The photograph was taken at an angle · symptoms reported: itching and burning · the affected area is the sole of the foot.
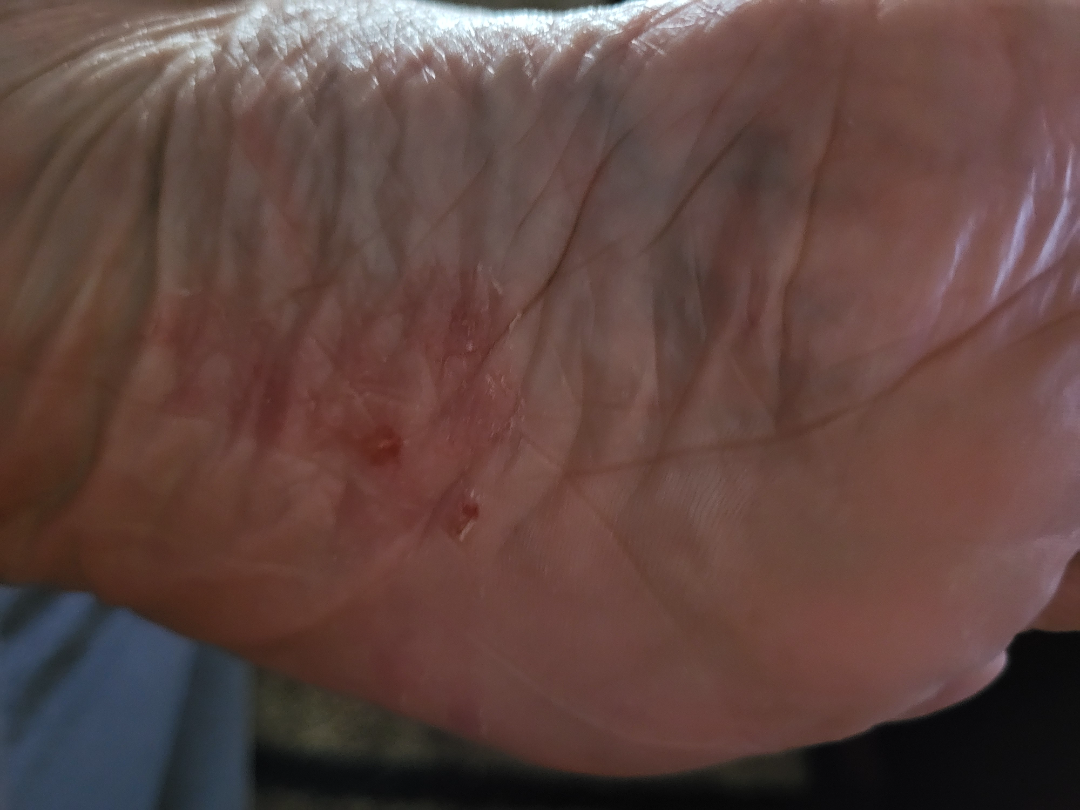<summary>
<differential>
  <leading>Tinea</leading>
</differential>
</summary>